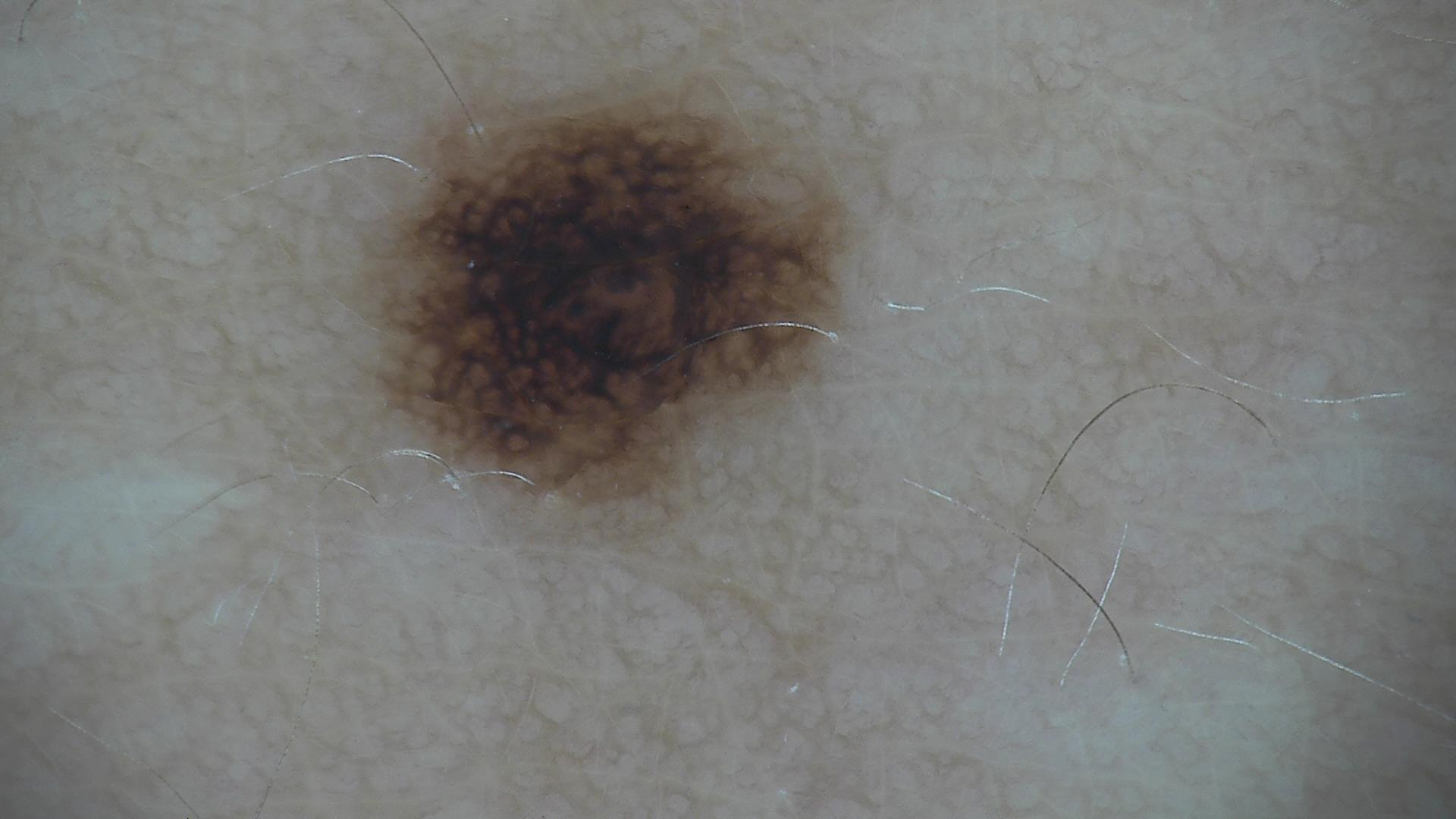modality: dermoscopy
label: dysplastic junctional nevus (expert consensus)